A dermoscopic photograph of a skin lesion: 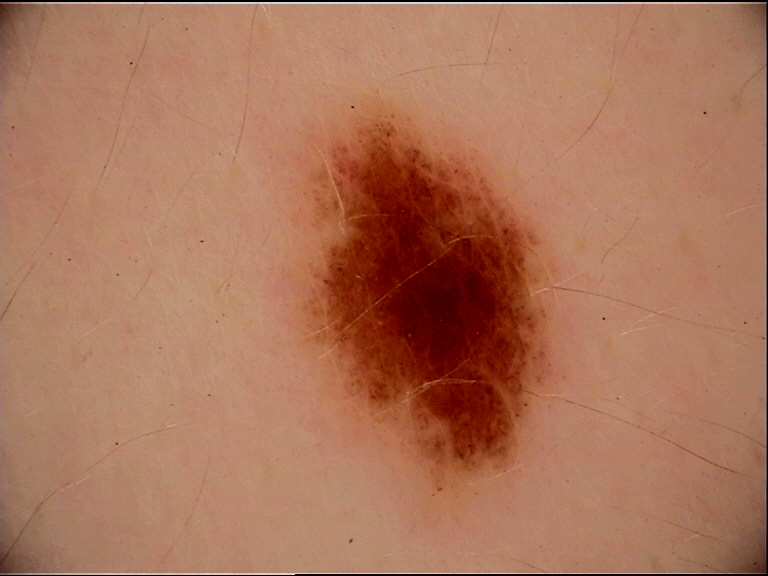Q: What was the diagnostic impression?
A: dysplastic junctional nevus (expert consensus)